The affected area is the back of the hand, this is a close-up image, the patient is a female aged 40–49:
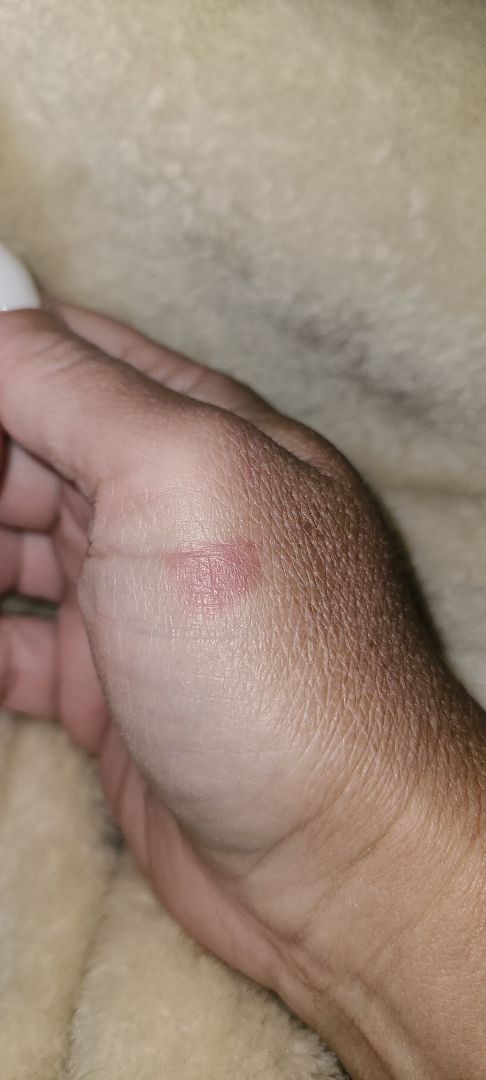  patient_category: a rash
  symptoms:
    - burning
    - bothersome appearance
  differential:
    leading:
      - Contact dermatitis
    unlikely:
      - Eczema
      - Burn erythema of back of hand
      - Acute dermatitis, NOS
      - Phytophotodermatitis
      - Irritant Contact Dermatitis